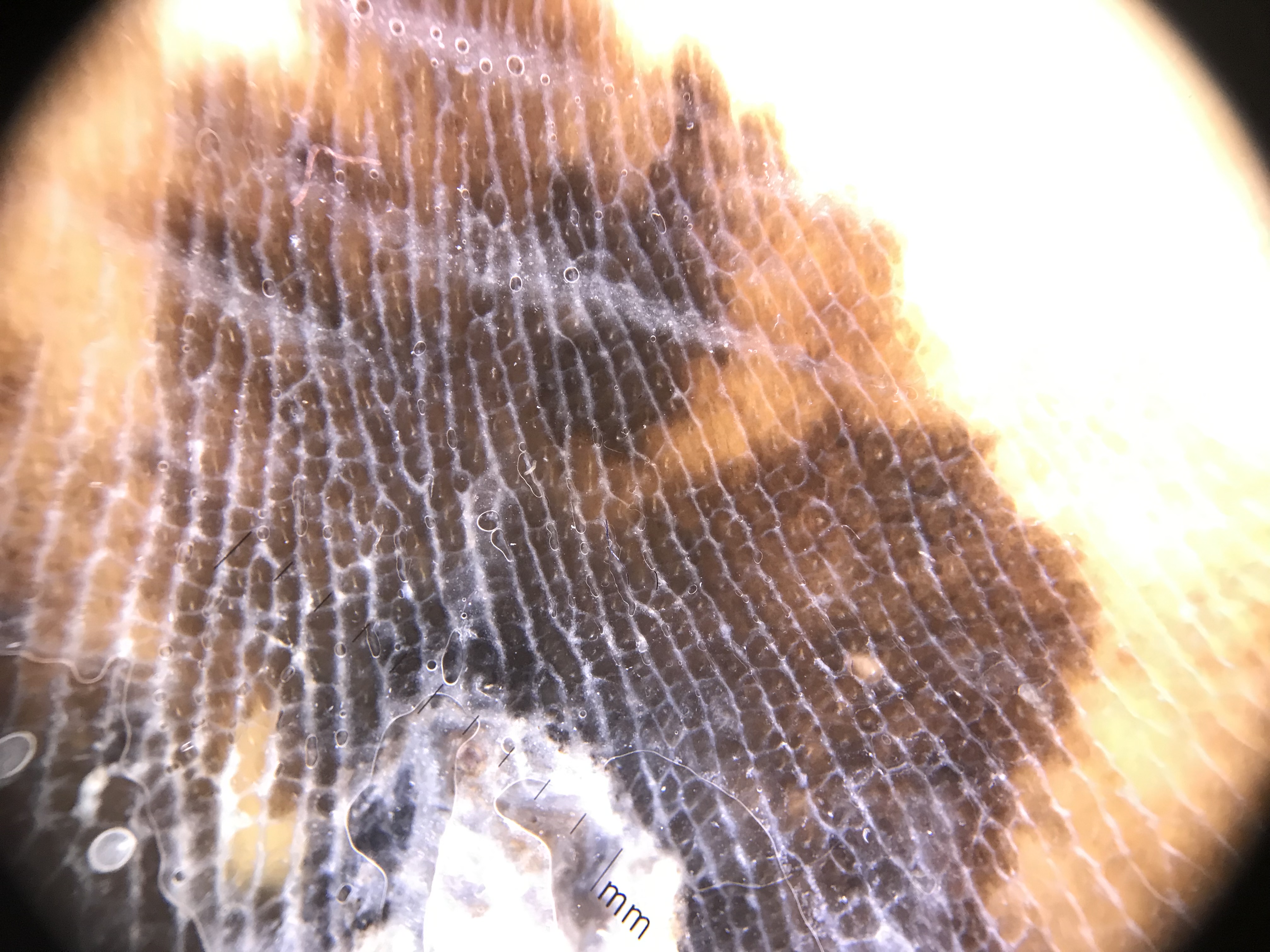Histopathologically confirmed as an acral lentiginous melanoma.